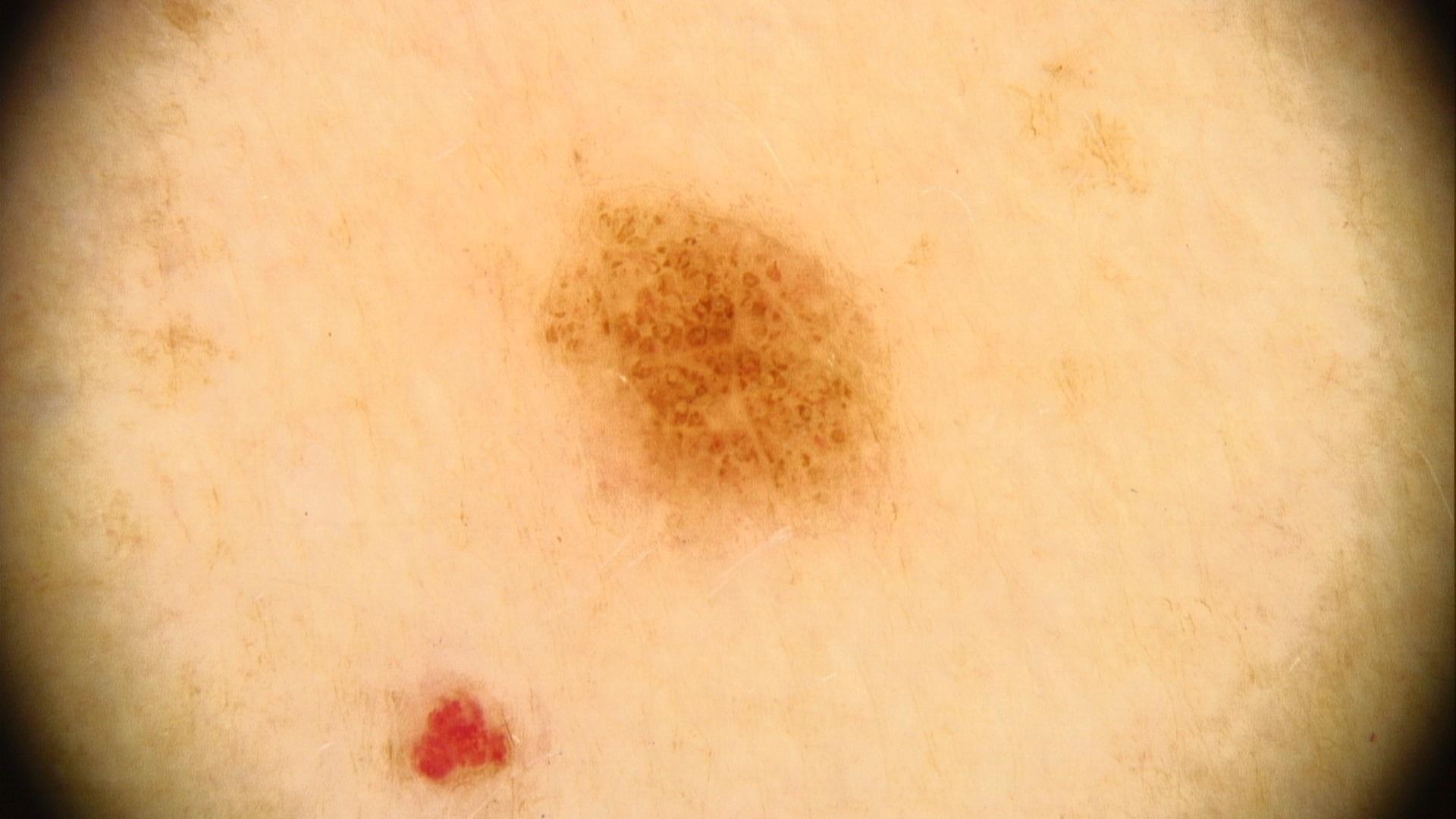Notes:
* relevant background: melanoma in a first-degree relative
* patient: male, in their 40s
* skin type: III
* assessment: Nevus